The photo was captured at an angle — 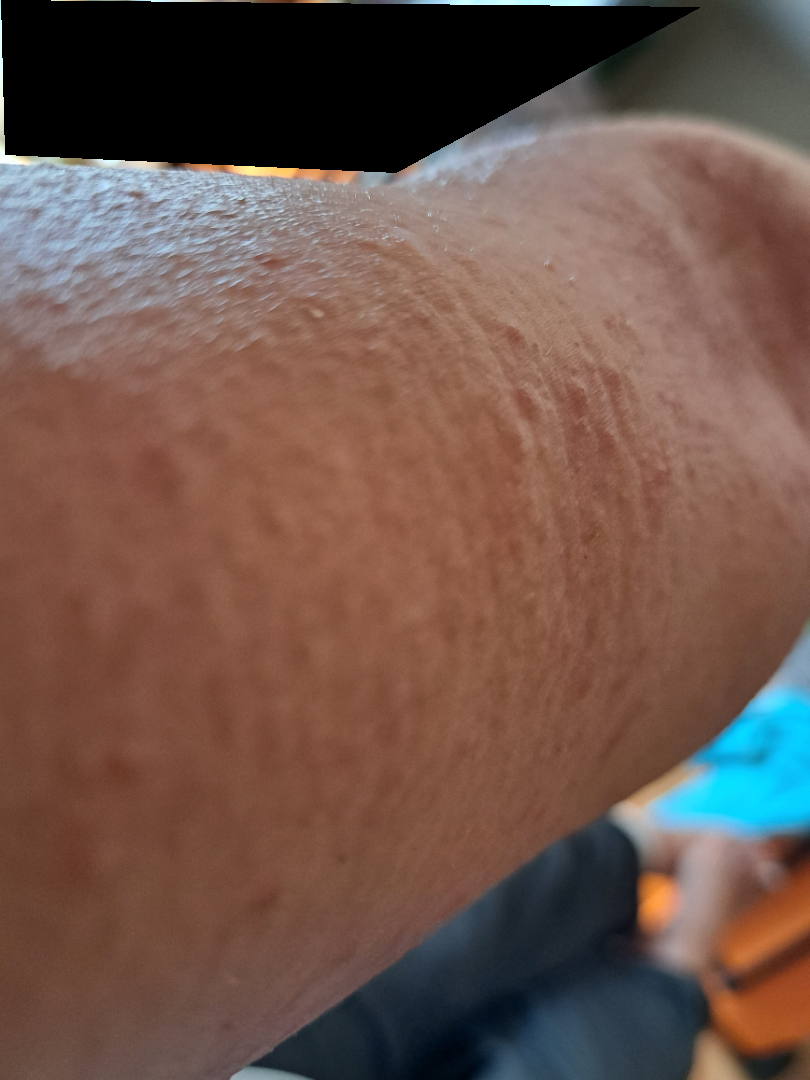The reviewing dermatologist was unable to assign a differential diagnosis from the image.